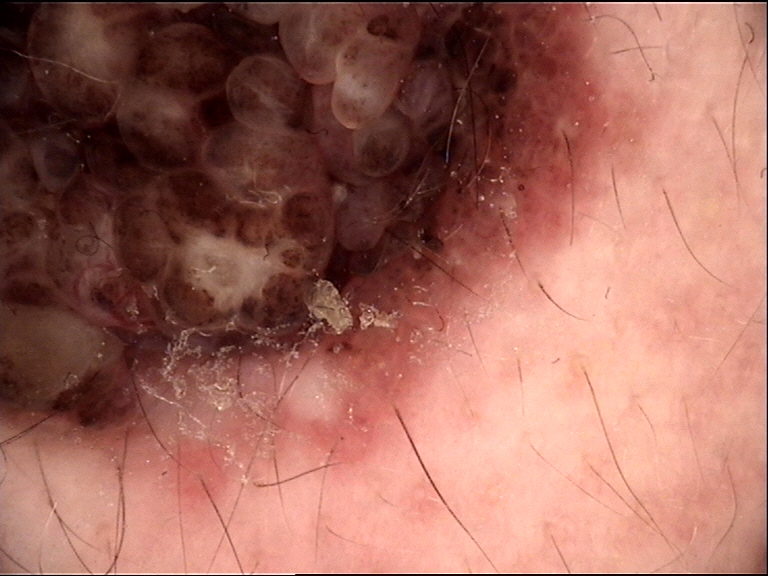Consistent with a congenital compound nevus.